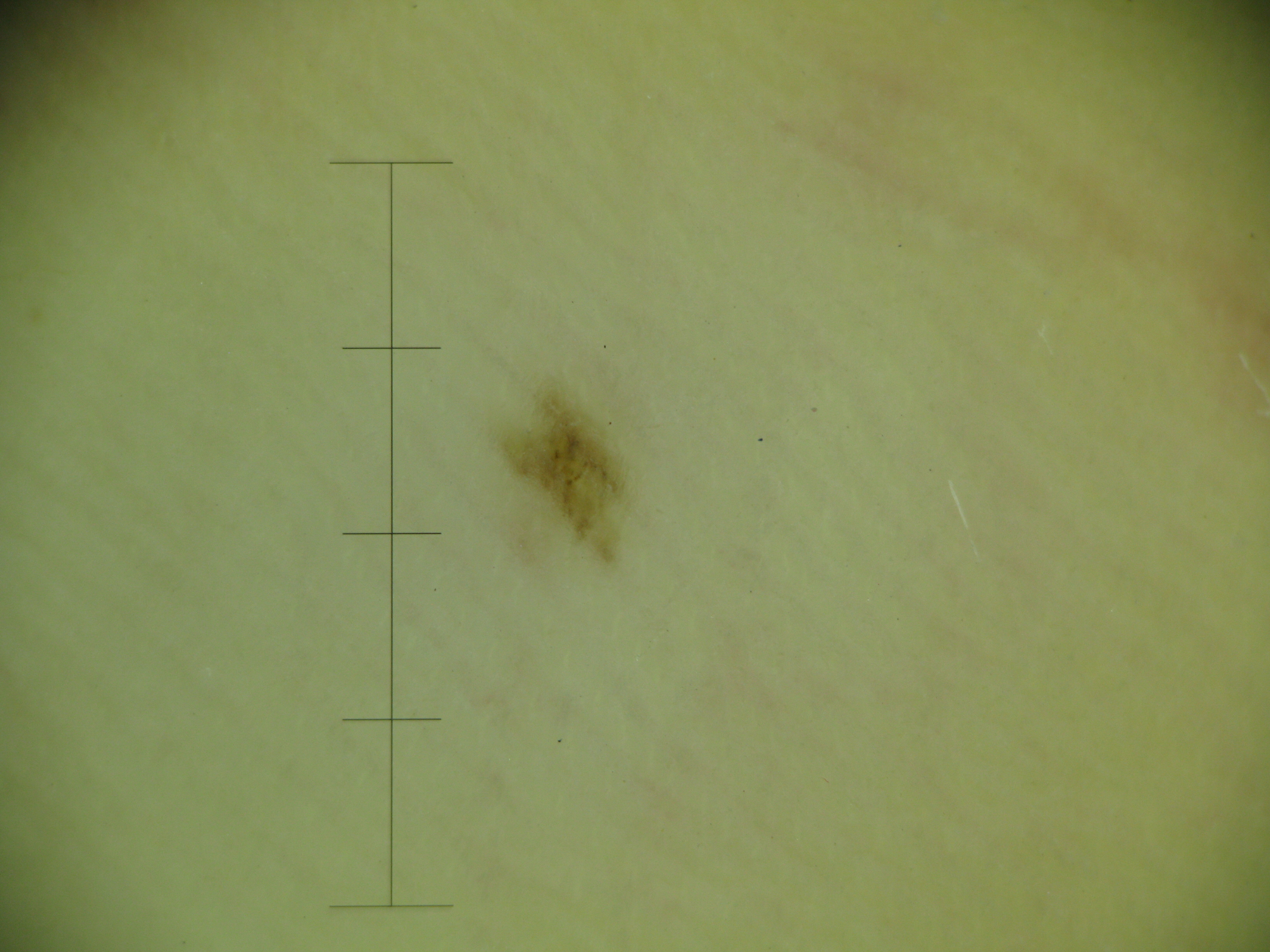The morphology is that of a banal lesion.
Consistent with an acral junctional nevus.